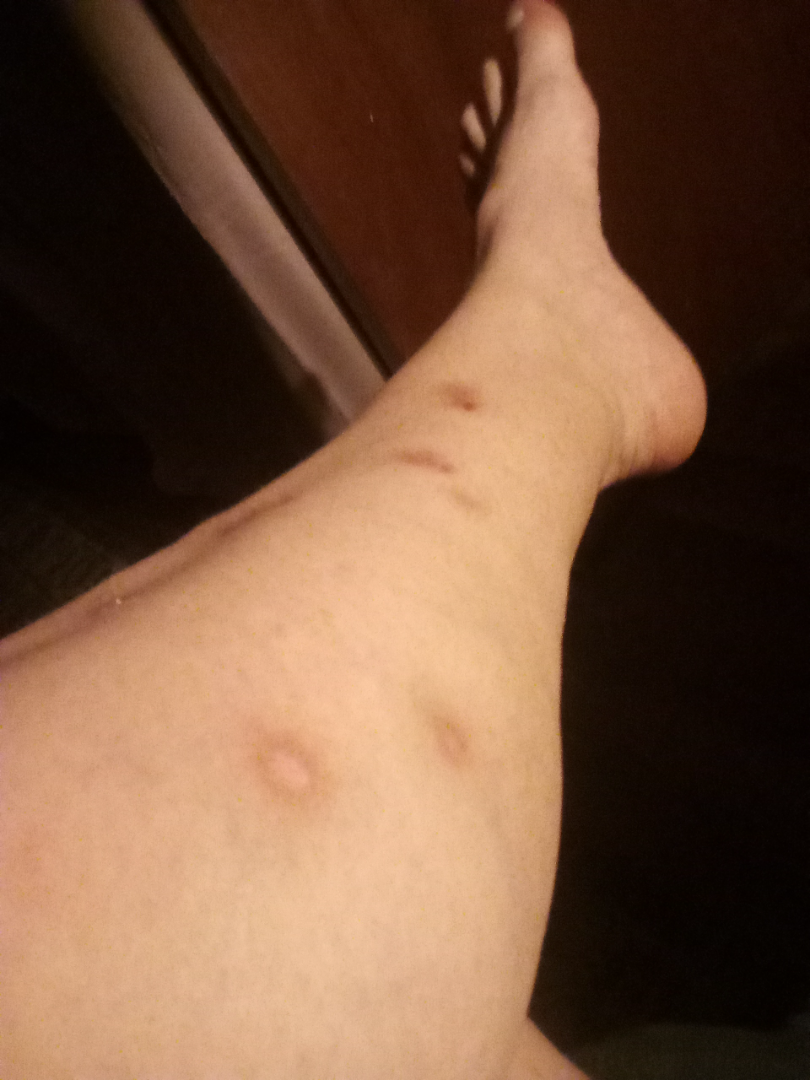Findings:
• assessment · indeterminate from the photograph